Close-up view. The head or neck is involved. The patient is a female aged 50–59 — 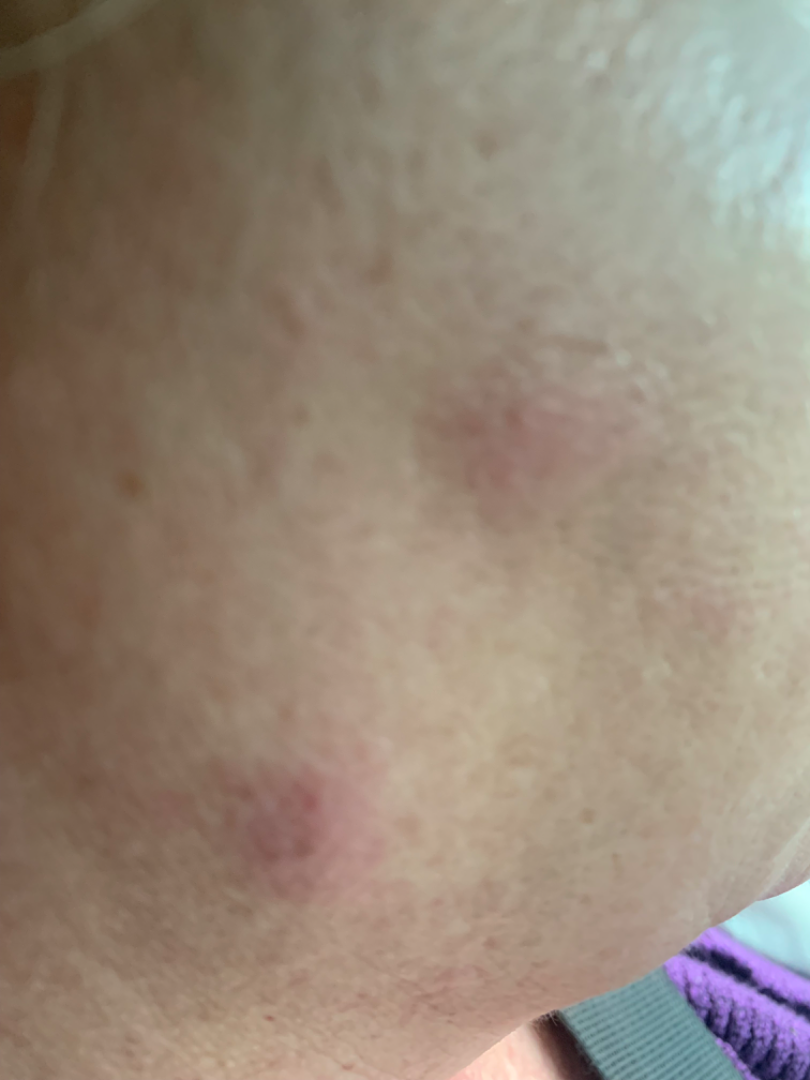No differential diagnosis could be assigned on photographic review.
No associated systemic symptoms reported.
Self-categorized by the patient as skin that appeared healthy to them.
The contributor reports the lesion is raised or bumpy.